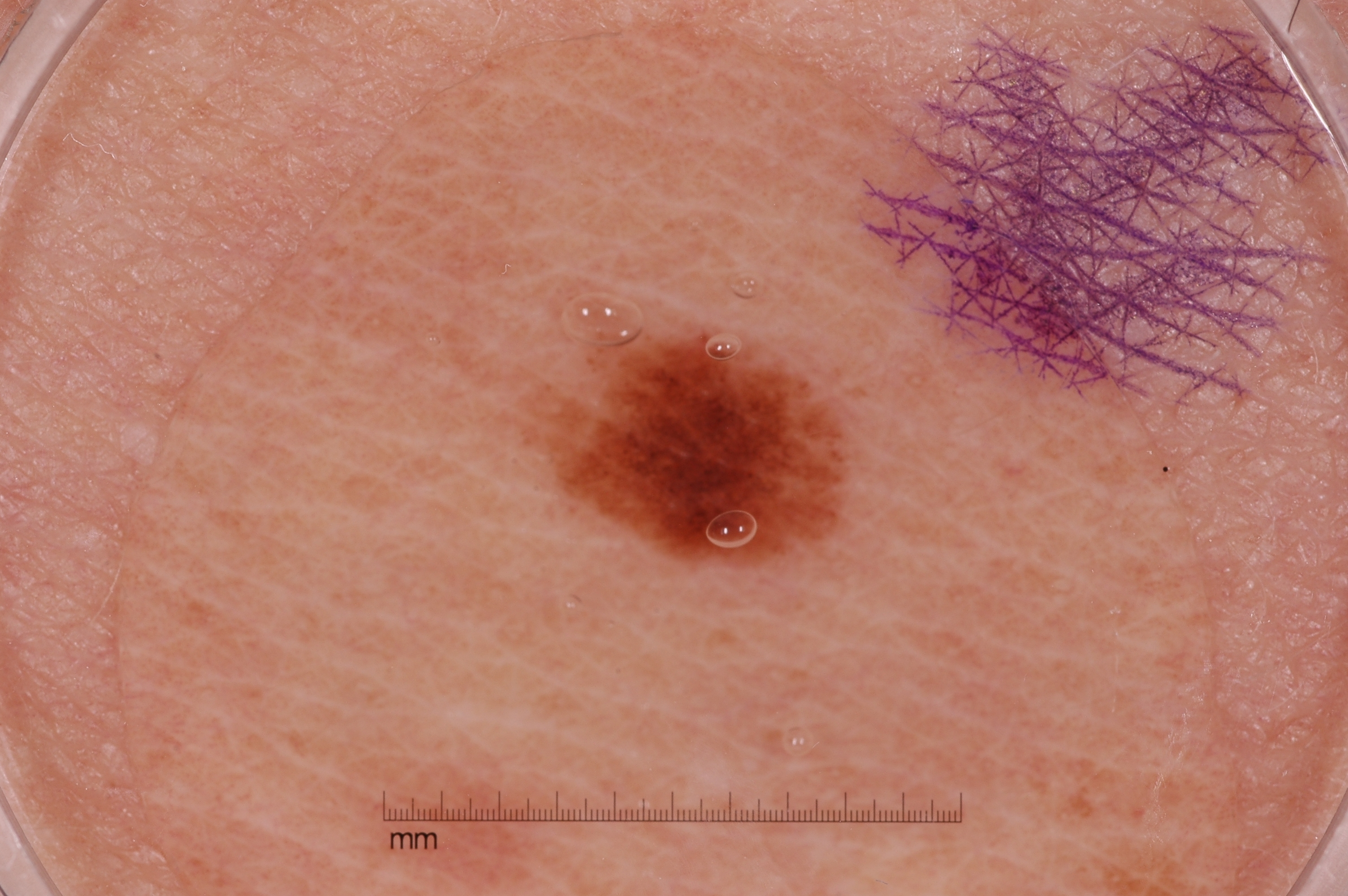A dermoscopic close-up of a skin lesion. The lesion covers approximately 4% of the dermoscopic field. Dermoscopic review identifies no streaks, milia-like cysts, negative network, or pigment network. In (x1, y1, x2, y2) order, the lesion spans [544,327,849,568]. The lesion was assessed as a melanocytic nevus, a benign skin lesion.